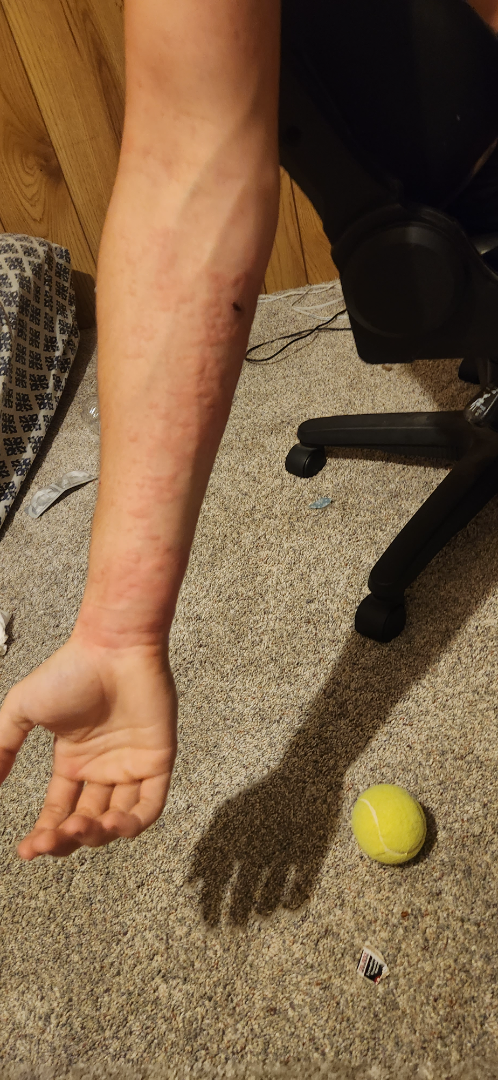An image taken at a distance.
No constitutional symptoms were reported.
The lesion is described as raised or bumpy.
The patient considered this a rash.
The contributor reports bothersome appearance, enlargement and itching.
Located on the arm.
Single-reviewer assessment: most likely Leukocytoclastic Vasculitis; with consideration of Calciphylaxis cutis; also consider Erythema multiforme.